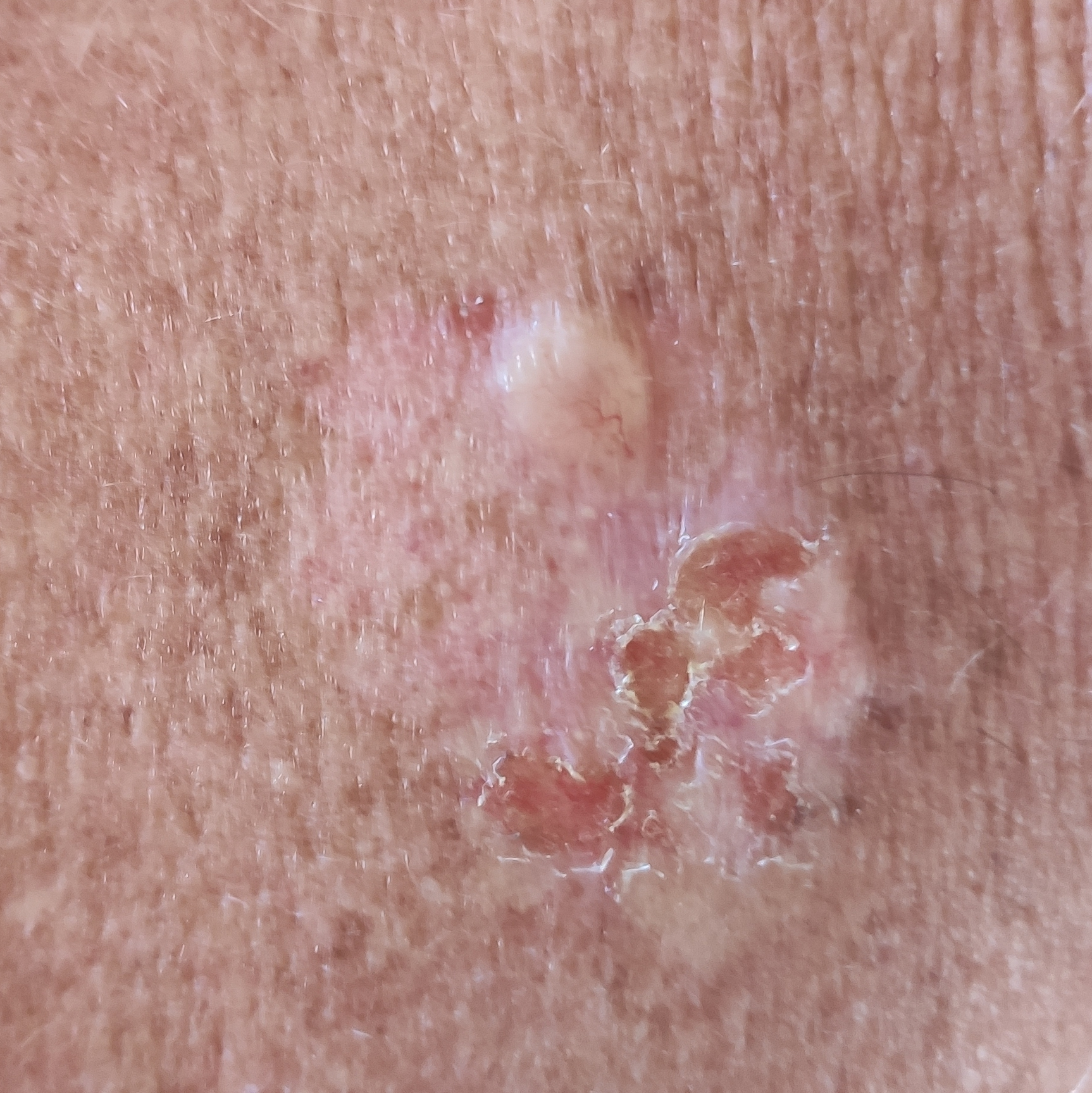A clinical photograph showing a skin lesion.
The patient reports that the lesion has grown, hurts, itches, has bled, and is elevated.
Biopsy-confirmed as a basal cell carcinoma.